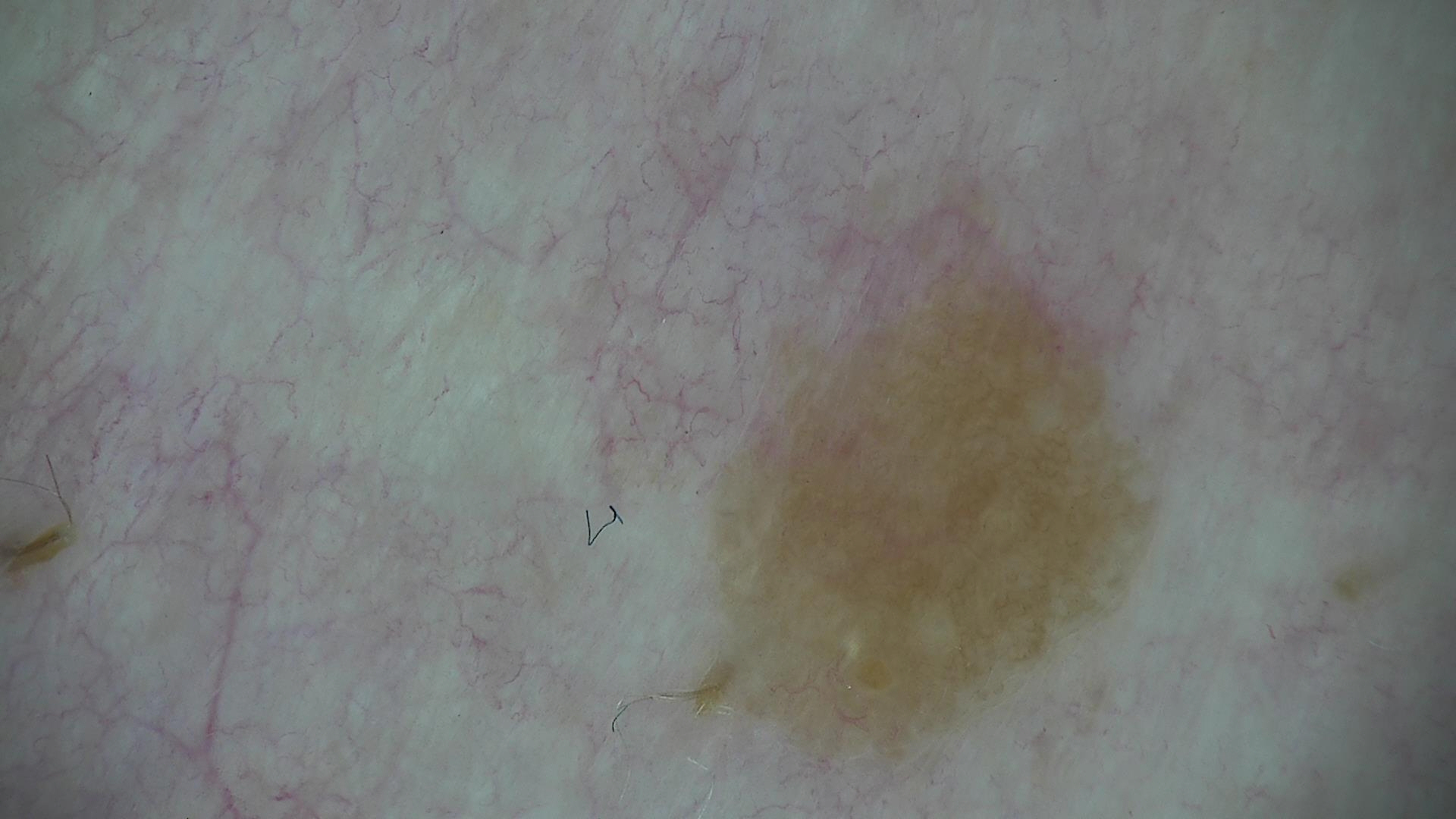Diagnosed as a benign lesion — a dysplastic junctional nevus.